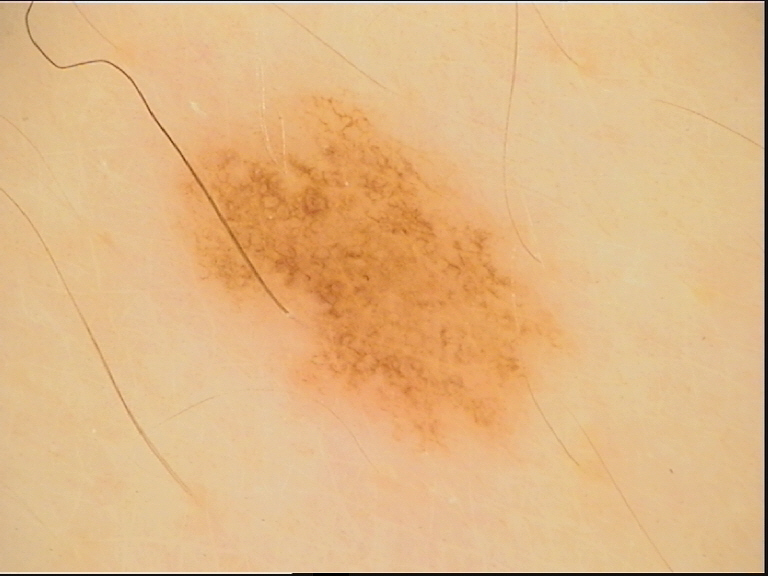A dermoscopy image of a single skin lesion. Consistent with a dysplastic junctional nevus.